Dermoscopy of a skin lesion:
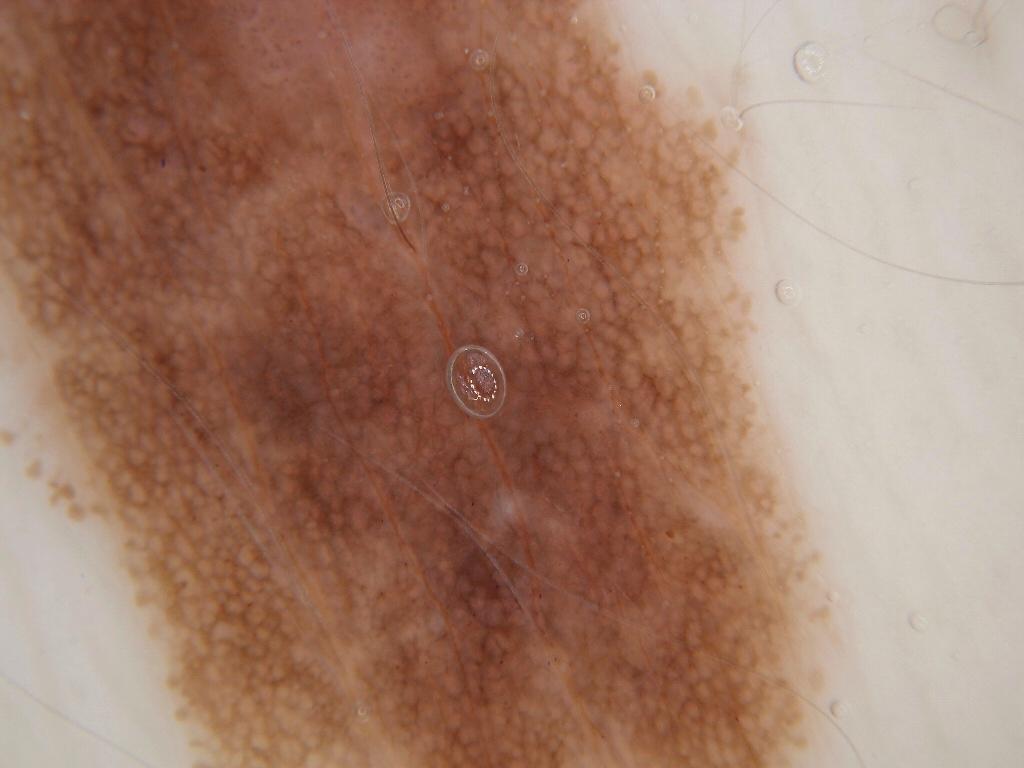dermoscopic features = streaks, globules, and pigment network | location = box(0, 0, 836, 763) | diagnosis = a melanocytic nevus.